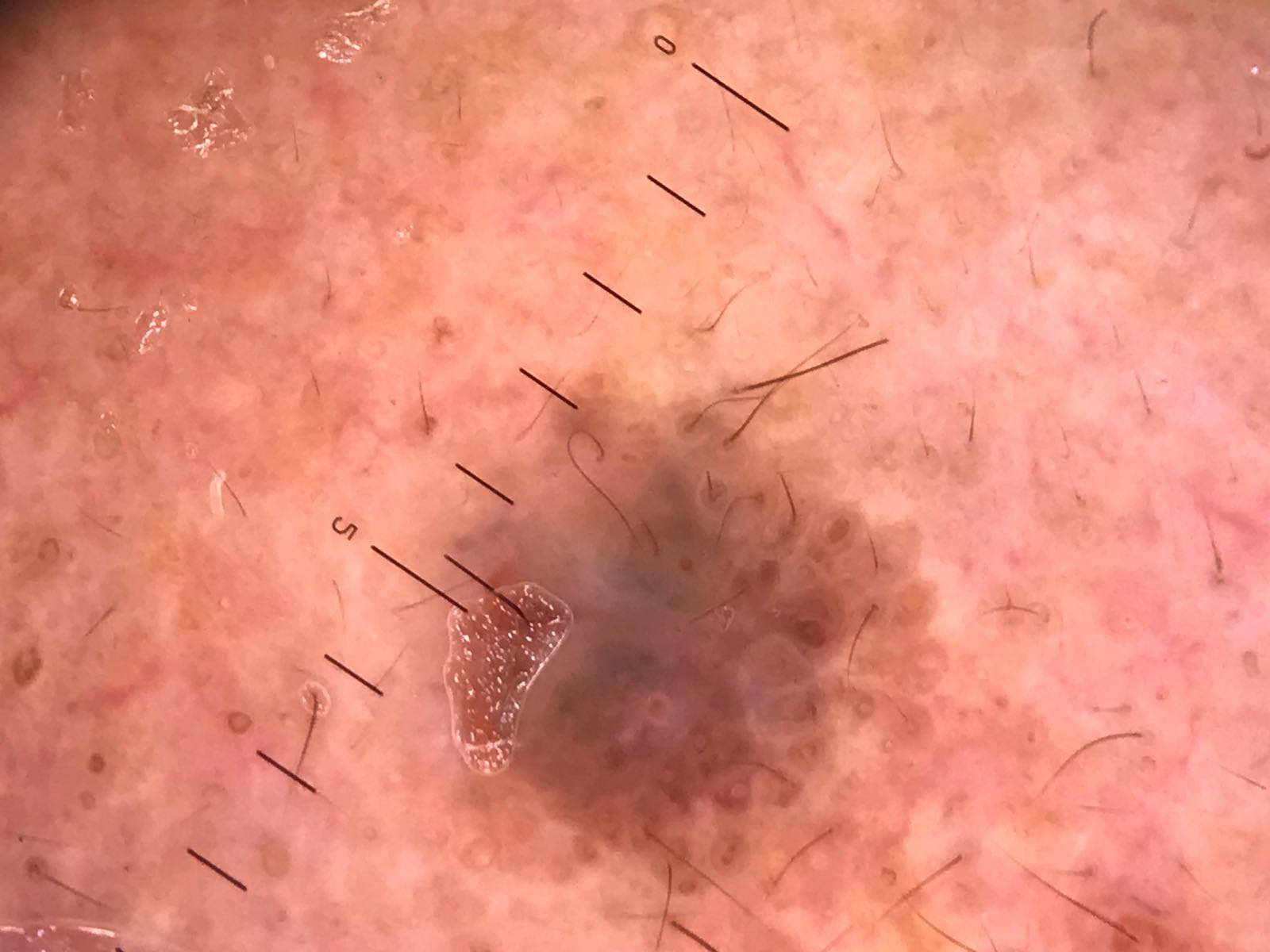category = keratinocytic, label = seborrheic keratosis (expert consensus).